A dermatoscopic image of a skin lesion.
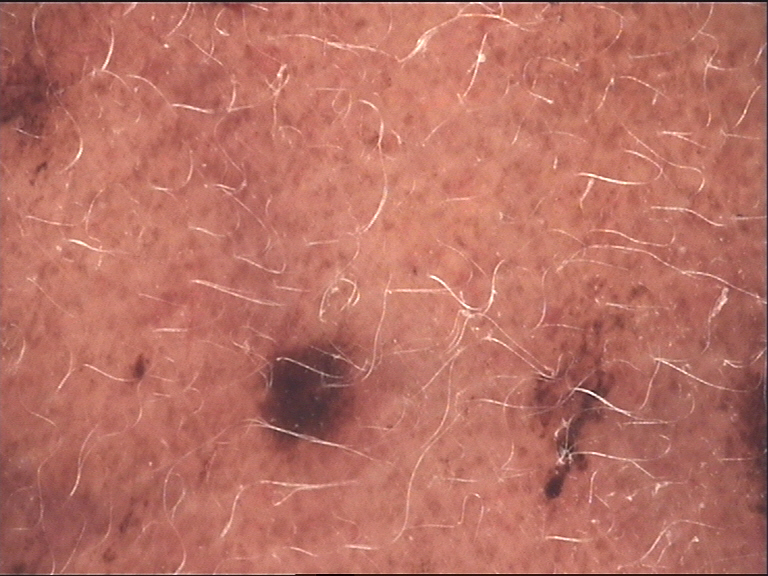This is a banal lesion.
The diagnosis was a congenital compound nevus.